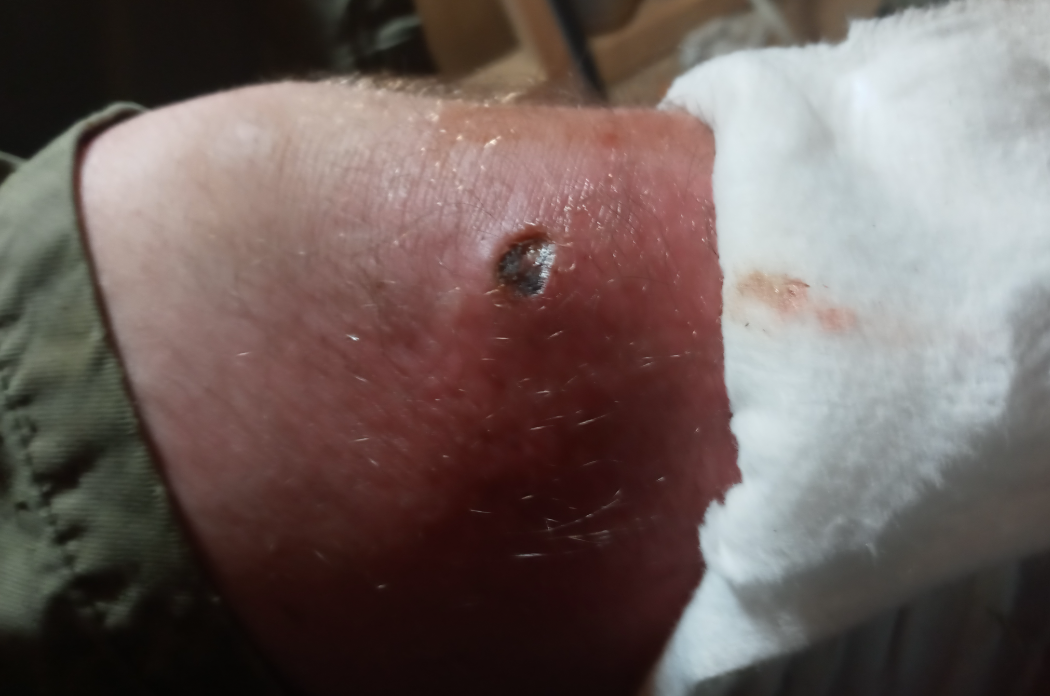Background:
The photograph was taken at an angle. The lesion is described as fluid-filled and raised or bumpy. The leg is involved. Associated systemic symptoms include fever, joint pain, fatigue and shortness of breath. The contributor is male.
Findings:
On teledermatology review: the leading consideration is Ecthyma; also on the differential is Abrasion, scrape, or scab; also raised was Abscess.